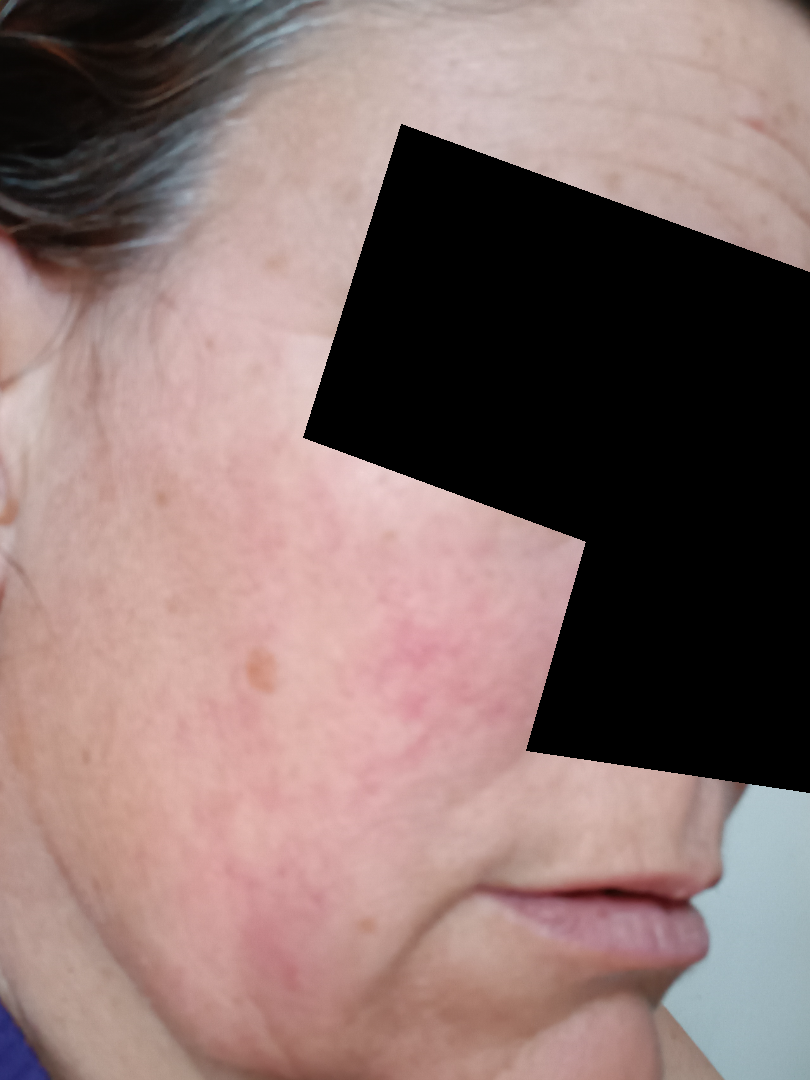Patient information:
Self-categorized by the patient as a rash. Texture is reported as rough or flaky, raised or bumpy and flat. The patient is 40–49, female. Present for more than five years. The patient indicates pain, enlargement, darkening, burning, bothersome appearance and itching. The photograph is a close-up of the affected area.